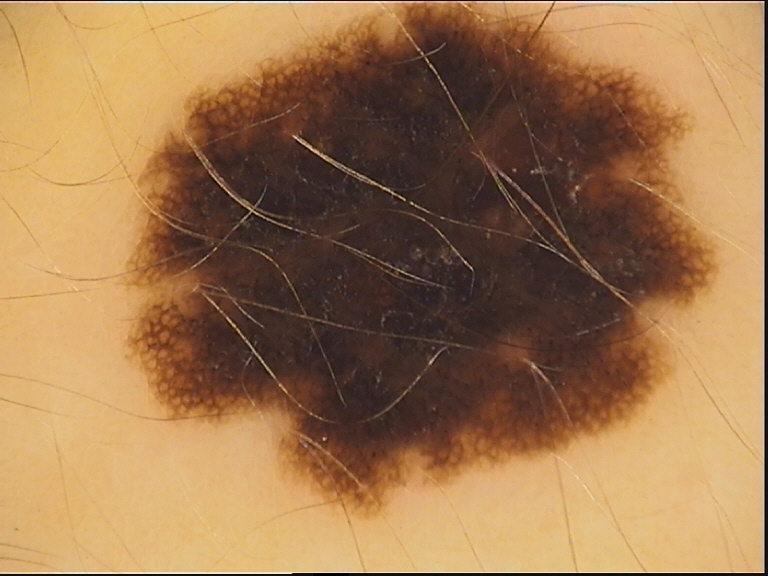<dermoscopy>
  <image>dermoscopy</image>
  <diagnosis>
    <name>dysplastic compound nevus</name>
    <code>cd</code>
    <malignancy>benign</malignancy>
    <super_class>melanocytic</super_class>
    <confirmation>expert consensus</confirmation>
  </diagnosis>
</dermoscopy>